Close-up view, the back of the hand is involved, the patient considered this a rash, reported duration is one to four weeks, skin tone: Fitzpatrick IV; lay reviewers estimated Monk Skin Tone 5 (US pool) or 3 (India pool).
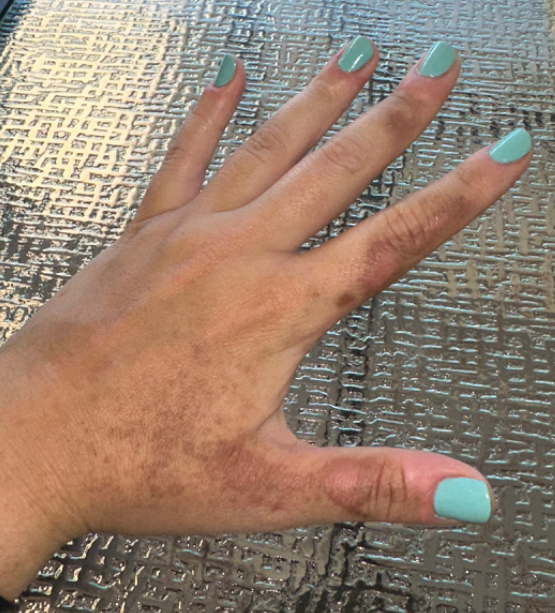Case summary:
- impression · reviewed remotely by one dermatologist: most likely Hyperpigmentation; an alternative is Photodermatitis; a remote consideration is Kaposi's sarcoma of skin